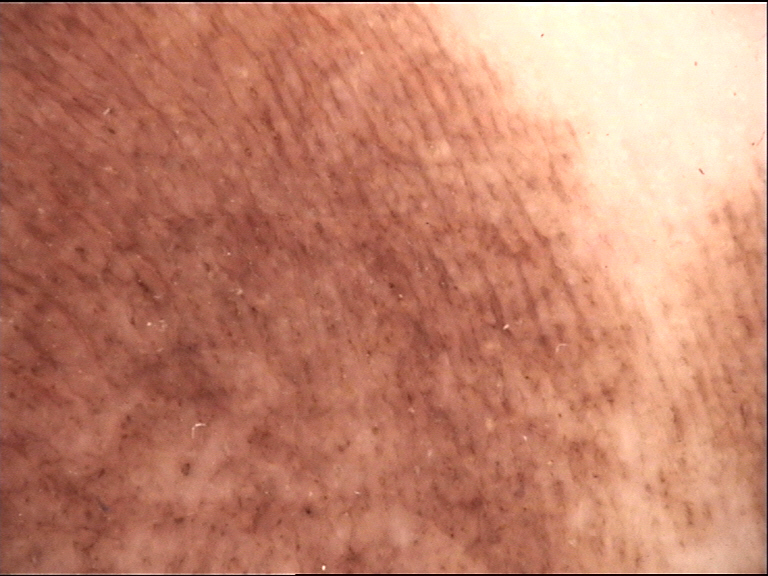assessment: acral compound nevus (expert consensus).